The patient was assessed as Fitzpatrick phototype I. The chart notes a previous melanoma — 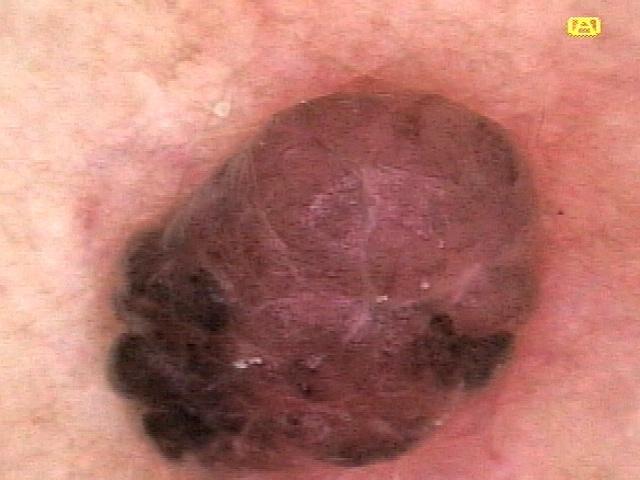anatomic site: the trunk | pathology: Melanoma (biopsy-proven).